A clinical overview photograph of a skin lesion. A female subject aged 33-37 — 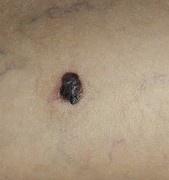Located on a lower extremity. Histopathological examination showed a melanoma.